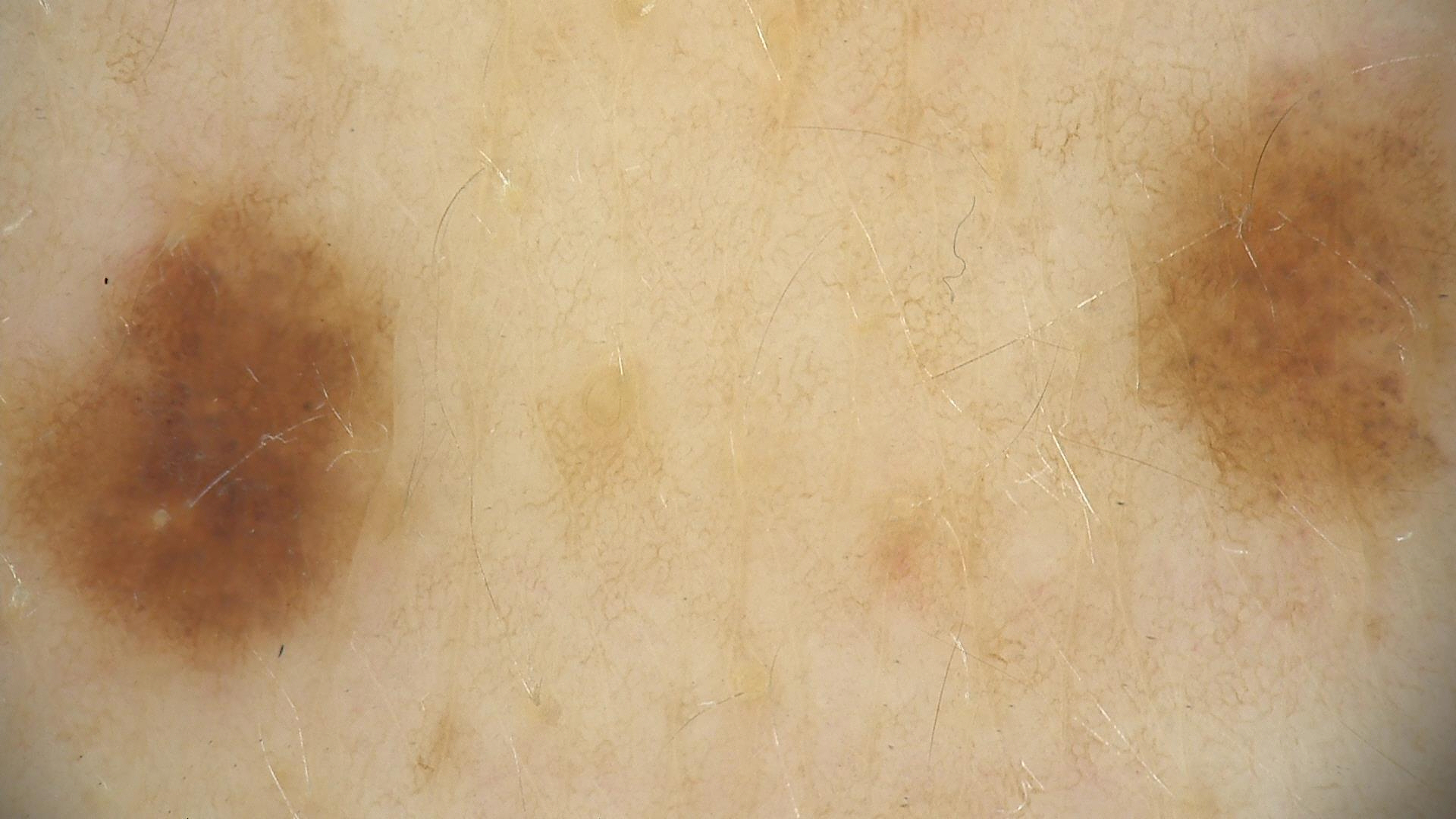Summary:
A dermoscopy image of a single skin lesion.
Conclusion:
Consistent with a dysplastic junctional nevus.